A dermoscopy image of a single skin lesion: 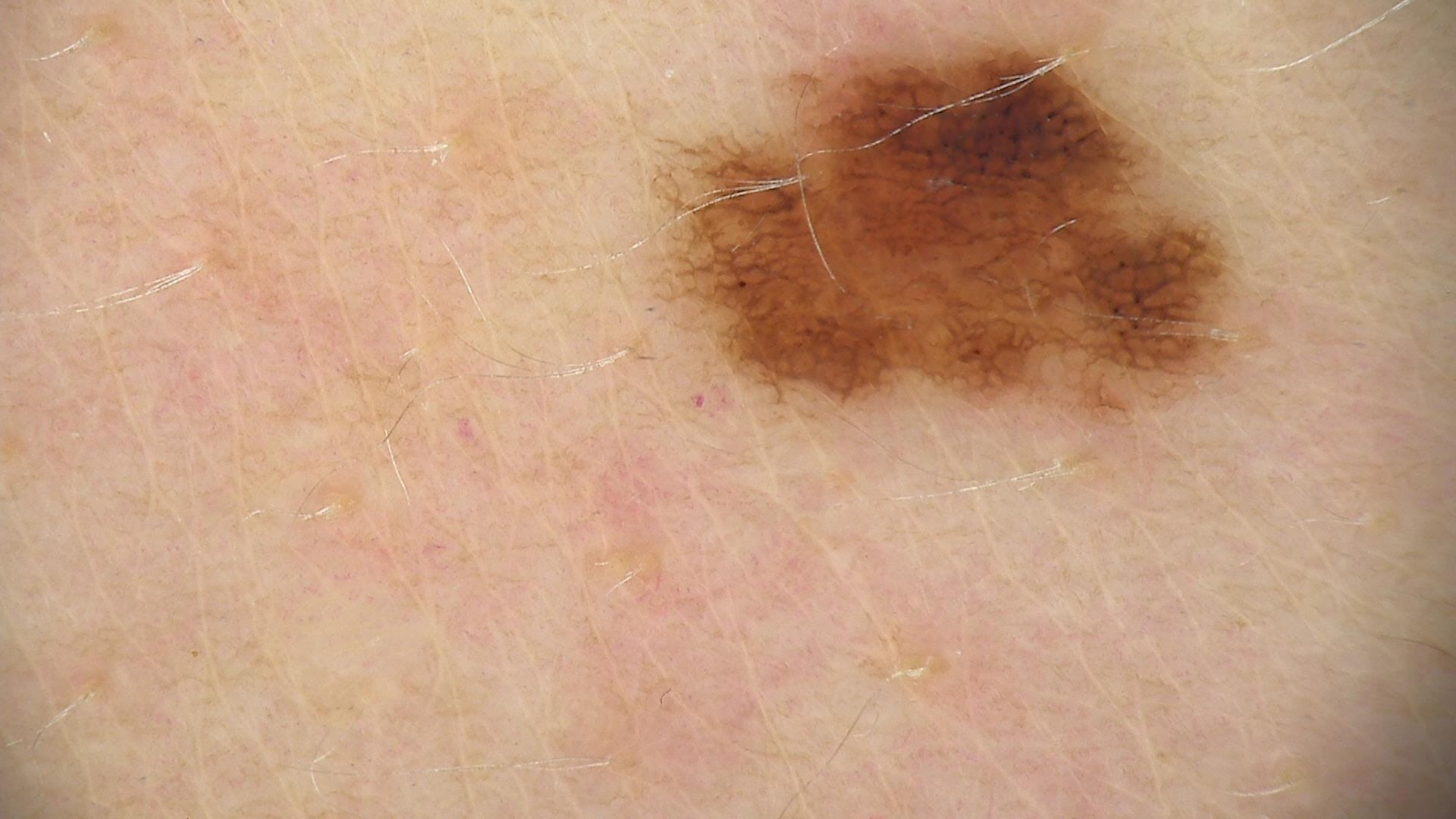Impression:
The diagnostic label was a benign lesion — a dysplastic junctional nevus.